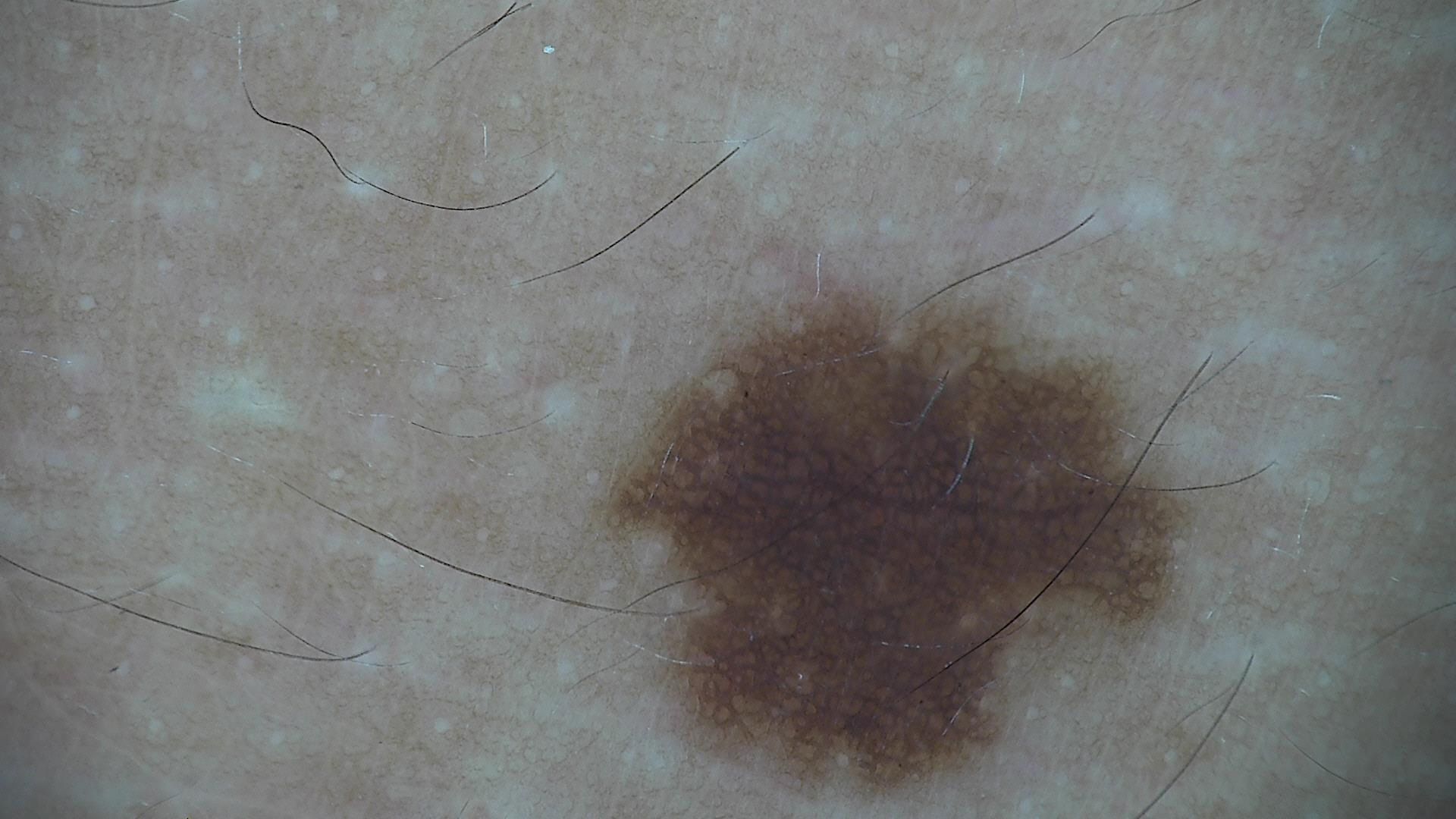modality = dermatoscopy, assessment = dysplastic junctional nevus (expert consensus).